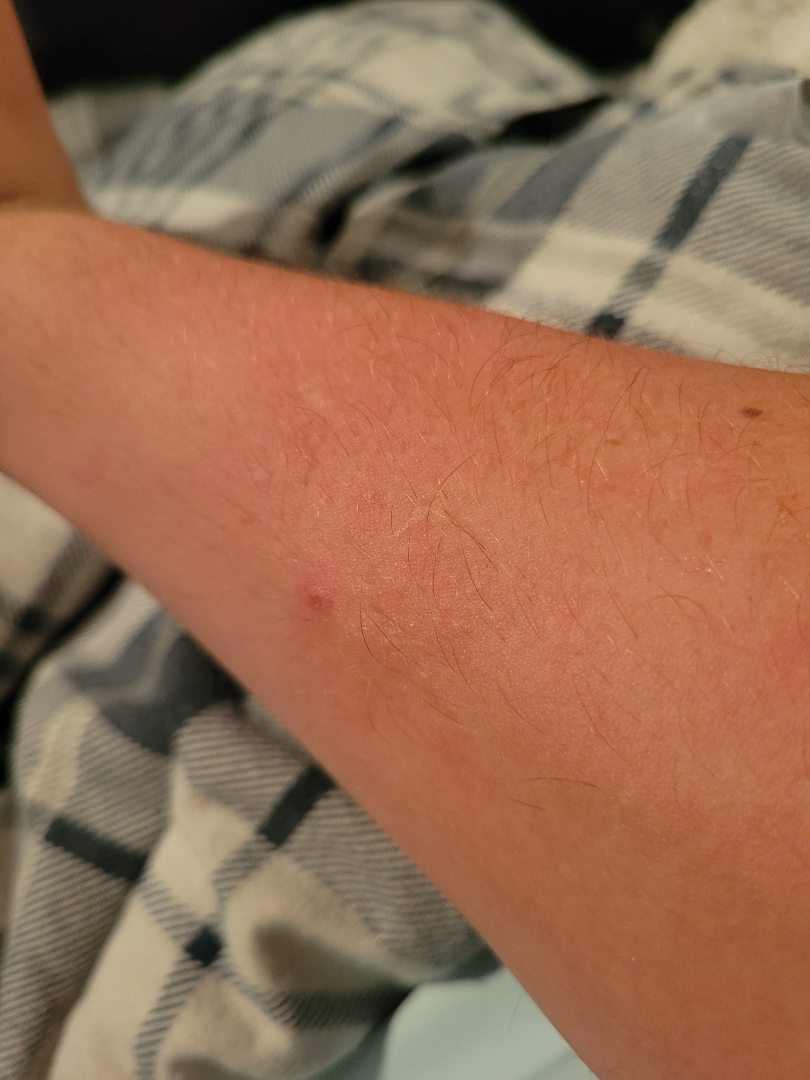The condition could not be reliably identified from the image. The photo was captured at a distance. The lesion involves the arm.